The photograph is a close-up of the affected area:
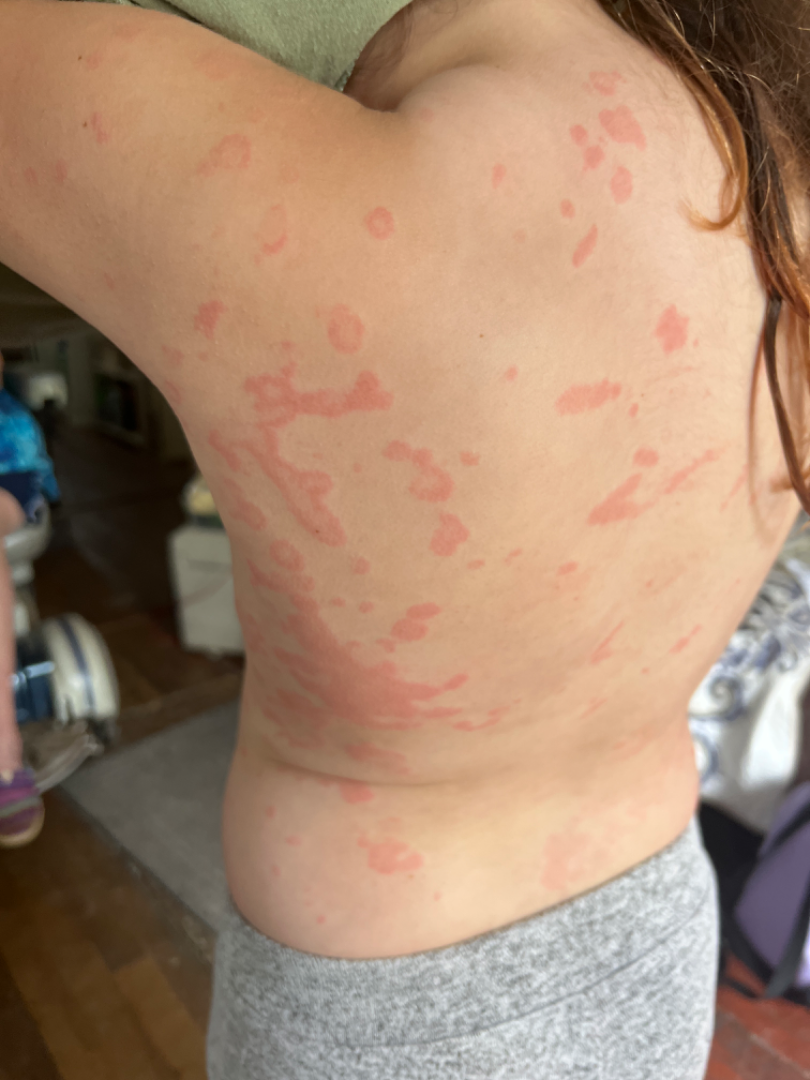Assessment:
Urticaria (most likely); Insect Bite (possible); Leukocytoclastic Vasculitis (possible).